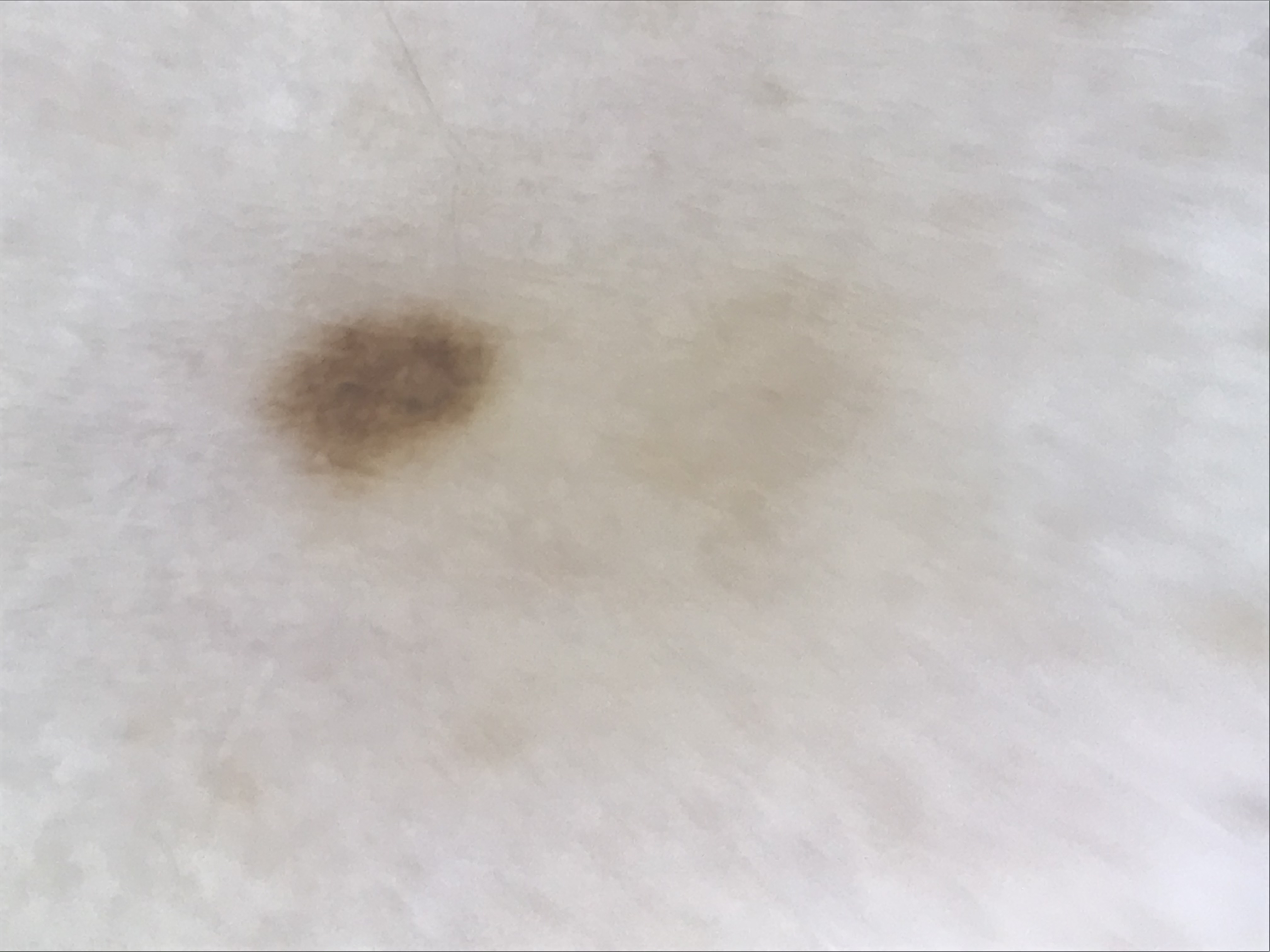image: dermatoscopy | diagnostic label: acral dysplastic junctional nevus (expert consensus).